The photograph was taken at an angle. The affected area is the front of the torso, arm, back of the torso and back of the hand. The contributor is 40–49, male.
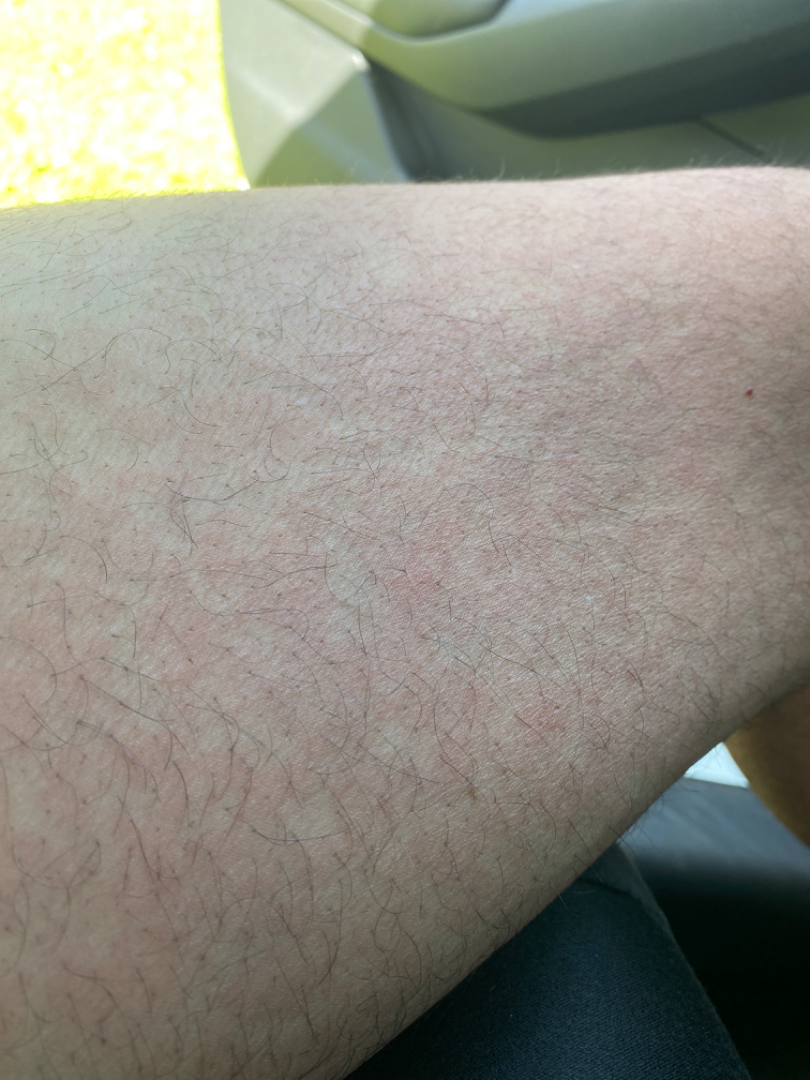The leading consideration is Drug Rash.